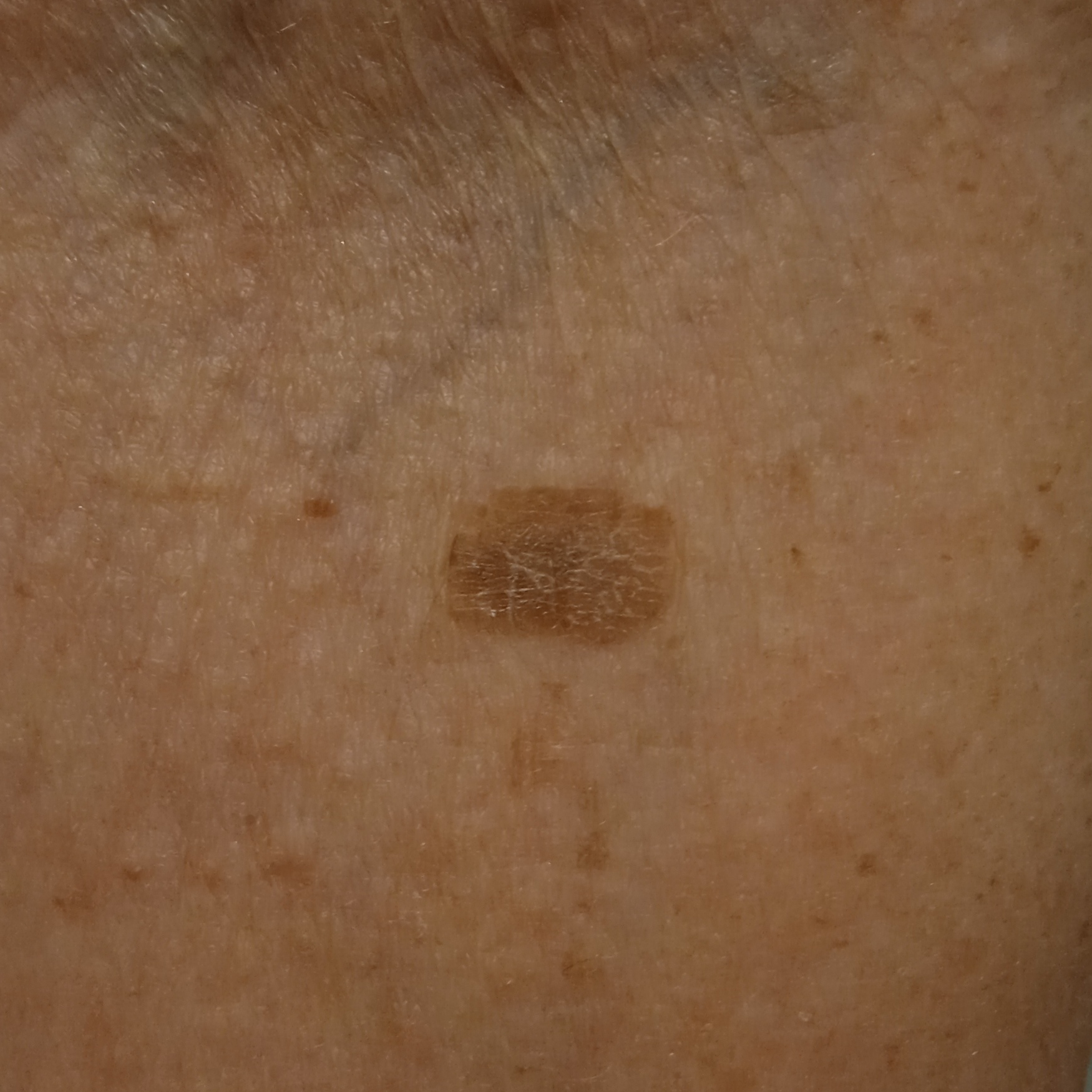Case:
– image · clinical photograph
– referral · research study (no referral diagnosis)
– patient · female, 84 years of age
– size · 11.2 mm
– diagnosis · seborrheic keratosis (dermatologist consensus)